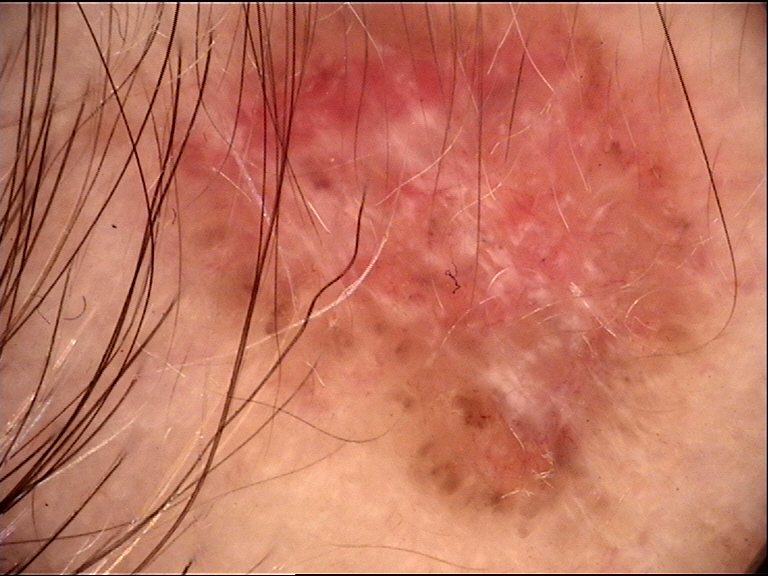The morphology is that of a keratinocytic lesion. Histopathologically confirmed as a malignancy — a basal cell carcinoma.